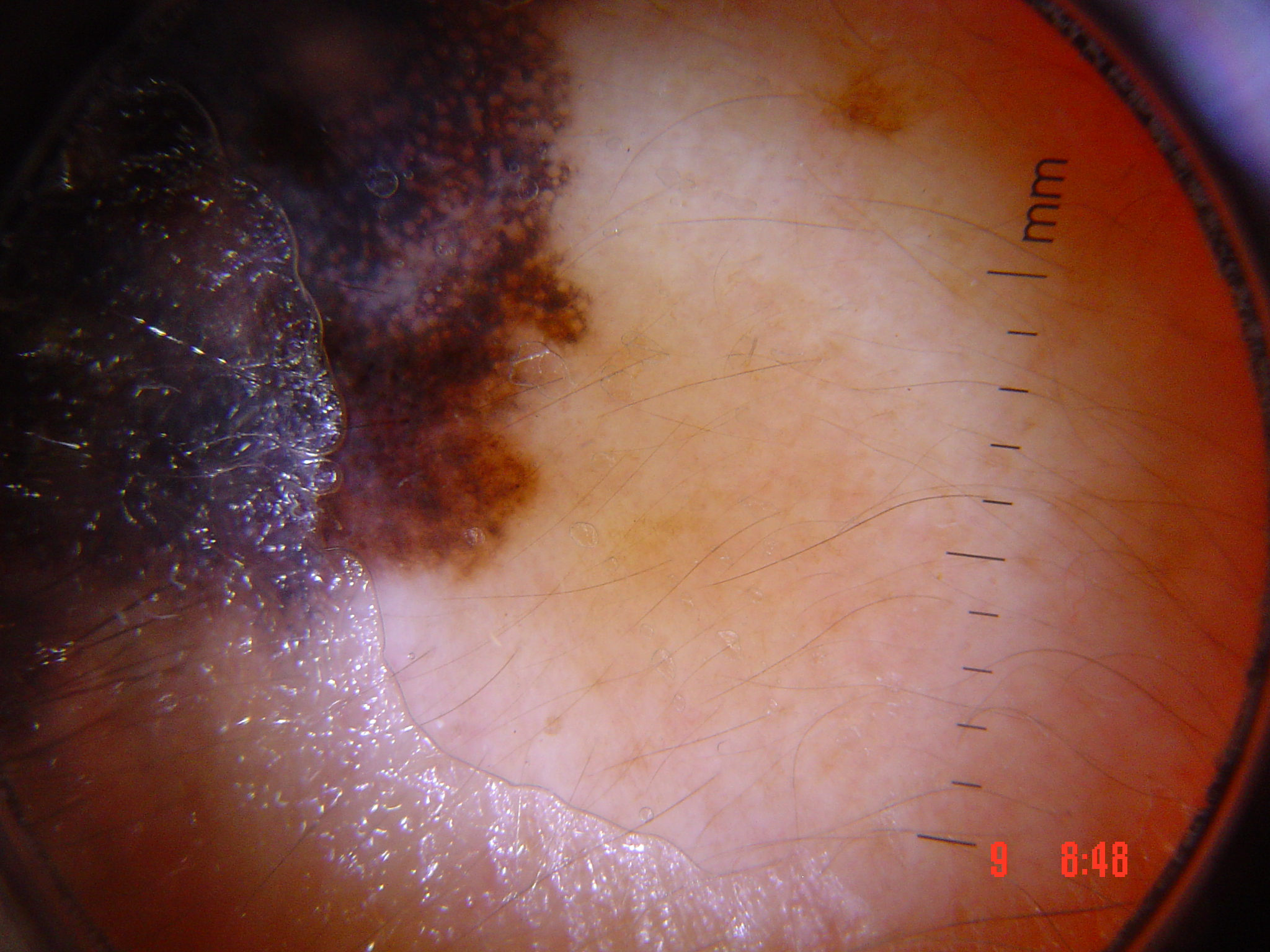{
  "diagnosis": {
    "name": "lentigo maligna",
    "code": "lm",
    "malignancy": "malignant",
    "super_class": "melanocytic",
    "confirmation": "histopathology"
  }
}